The photograph is a close-up of the affected area; the lesion involves the head or neck; the patient is male — 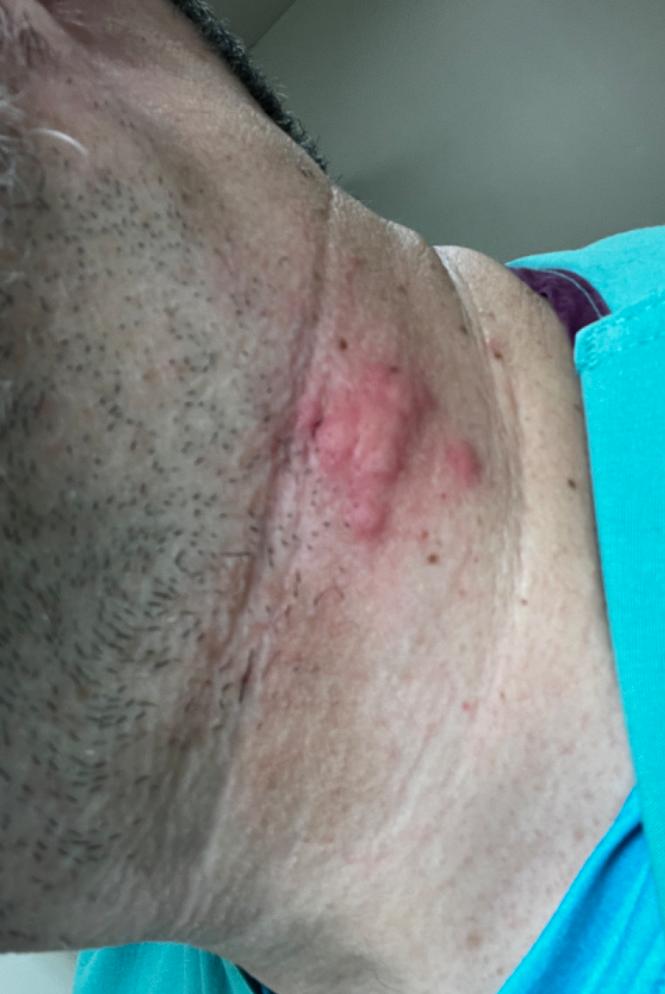Favoring B-Cell Cutaneous Lymphoma; possibly Dermatofibrosarcoma protuberans; less likely is Urticaria.